Reported lesion symptoms include pain and itching · the photo was captured at an angle · self-categorized by the patient as a rash · the back of the hand is involved · texture is reported as rough or flaky · the contributor is 18–29, male: 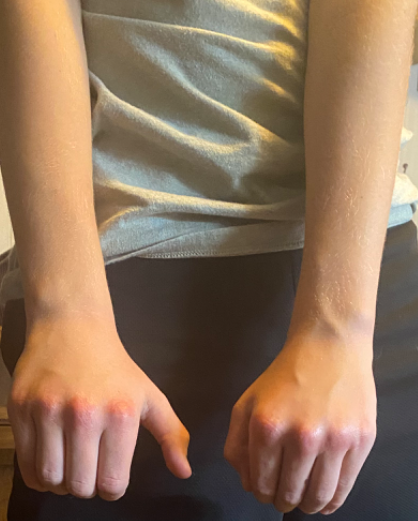Eczema (primary); Irritant Contact Dermatitis (considered); Autoimmune diseases affecting skin (lower probability).